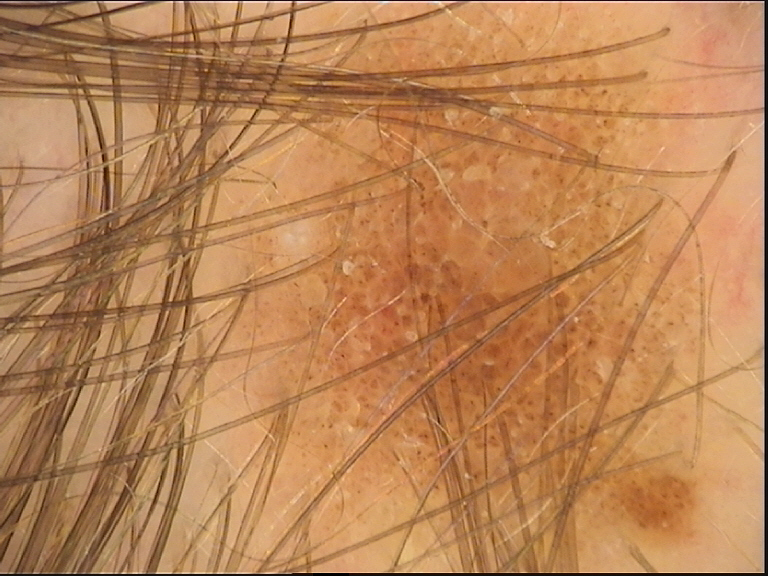The diagnostic label was a compound nevus.